A female subject in their early 80s.
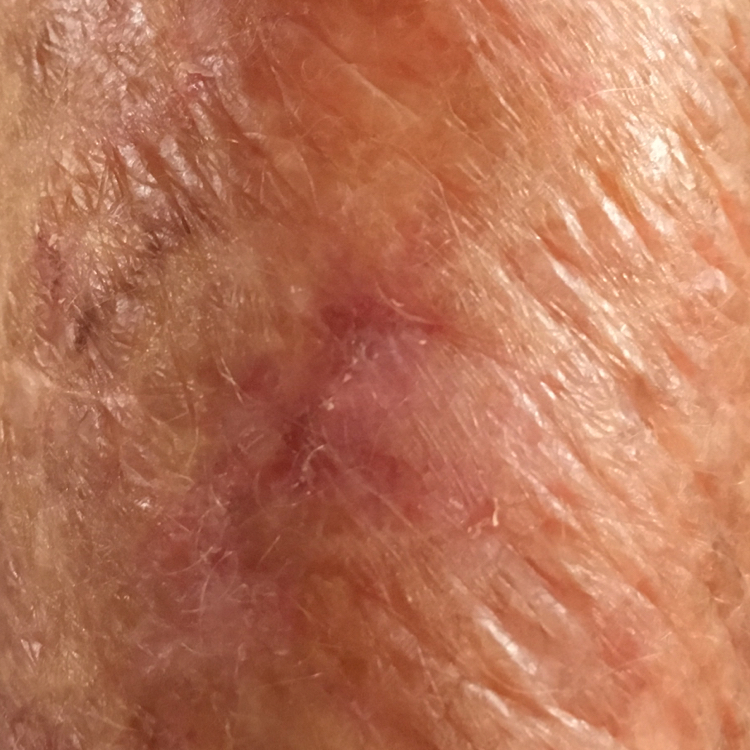Findings:
The lesion was found on a forearm. The patient describes that the lesion itches, but has not changed and has not bled.
Conclusion:
The diagnostic impression was an actinic keratosis.